The patient says their skin reddens with sun exposure · by self-report, a personal history of skin cancer and a personal history of cancer · a dermatoscopic image of a skin lesion · collected as part of a research study, without a referral diagnosis · a male patient aged 76: 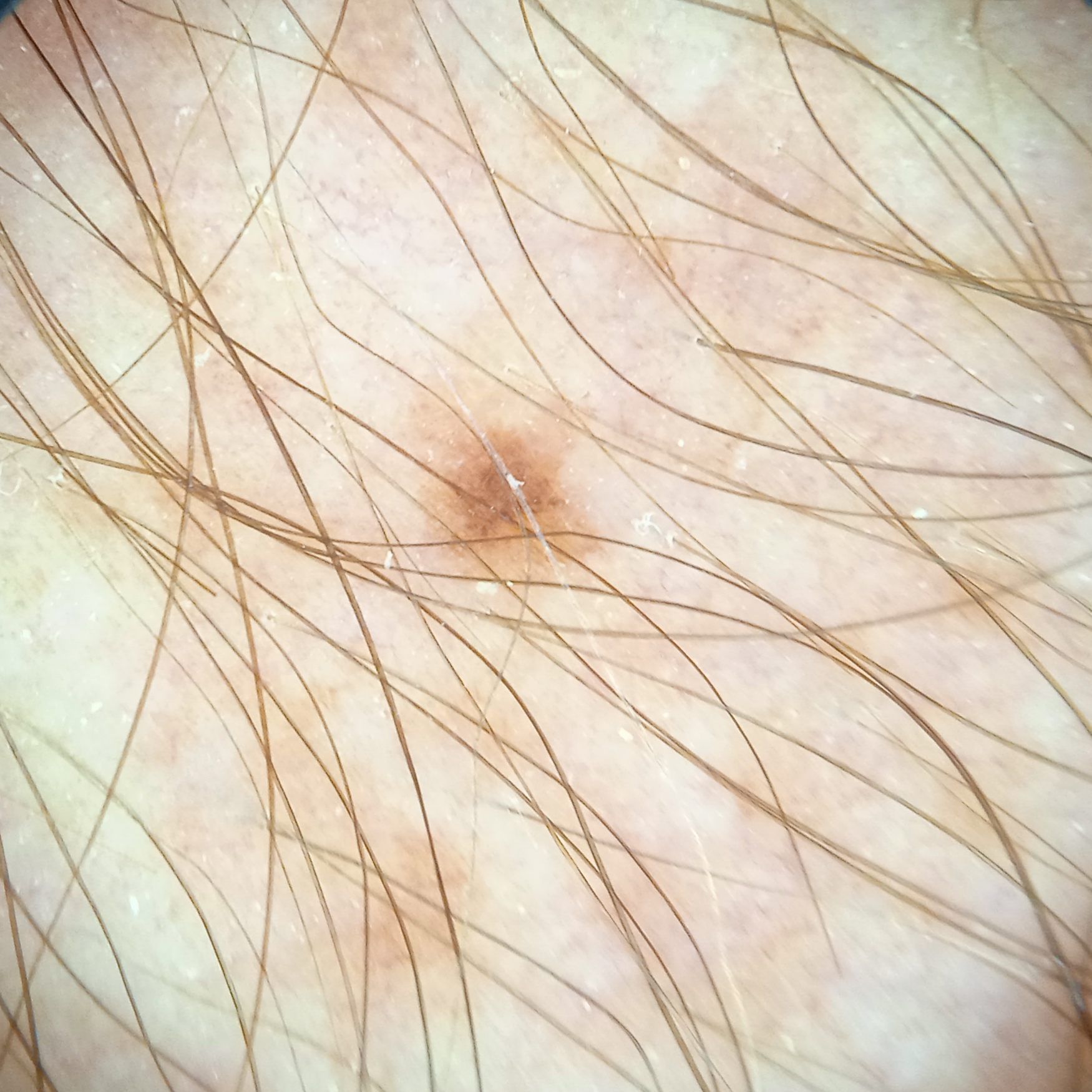Clinical context:
Located on an arm. The lesion is about 8.2 mm across.
Conclusion:
The diagnostic impression was a melanocytic nevus.